Dermoscopy of a skin lesion.
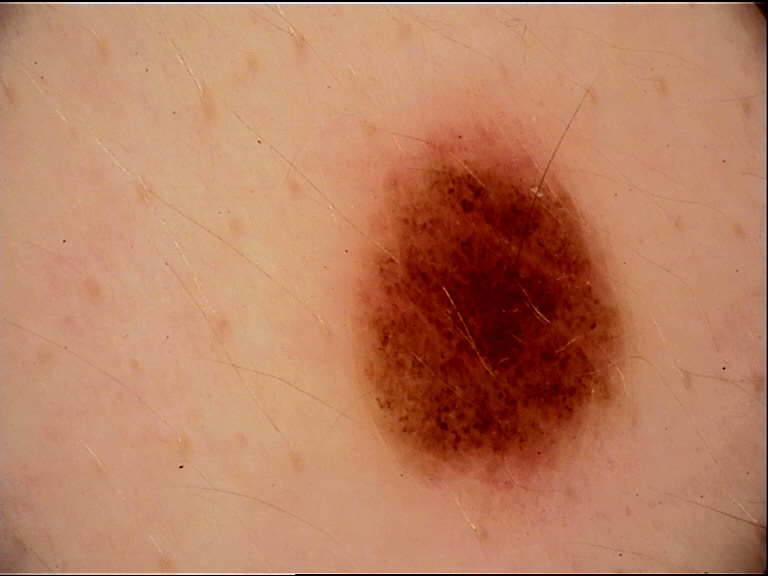The architecture is that of a banal lesion.
Consistent with a junctional nevus.